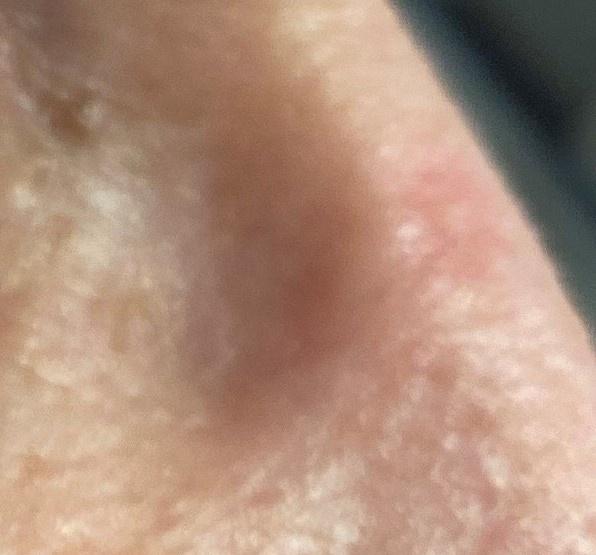| feature | finding |
|---|---|
| diagnostic label | Squamous cell carcinoma (biopsy-proven) |